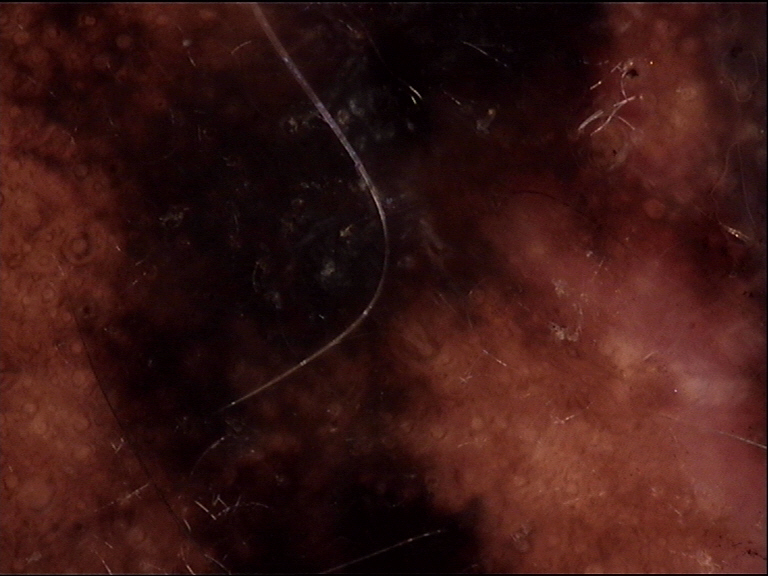{
  "image": "dermoscopy",
  "diagnosis": {
    "name": "lentigo maligna melanoma",
    "code": "lmm",
    "malignancy": "malignant",
    "super_class": "melanocytic",
    "confirmation": "histopathology"
  }
}